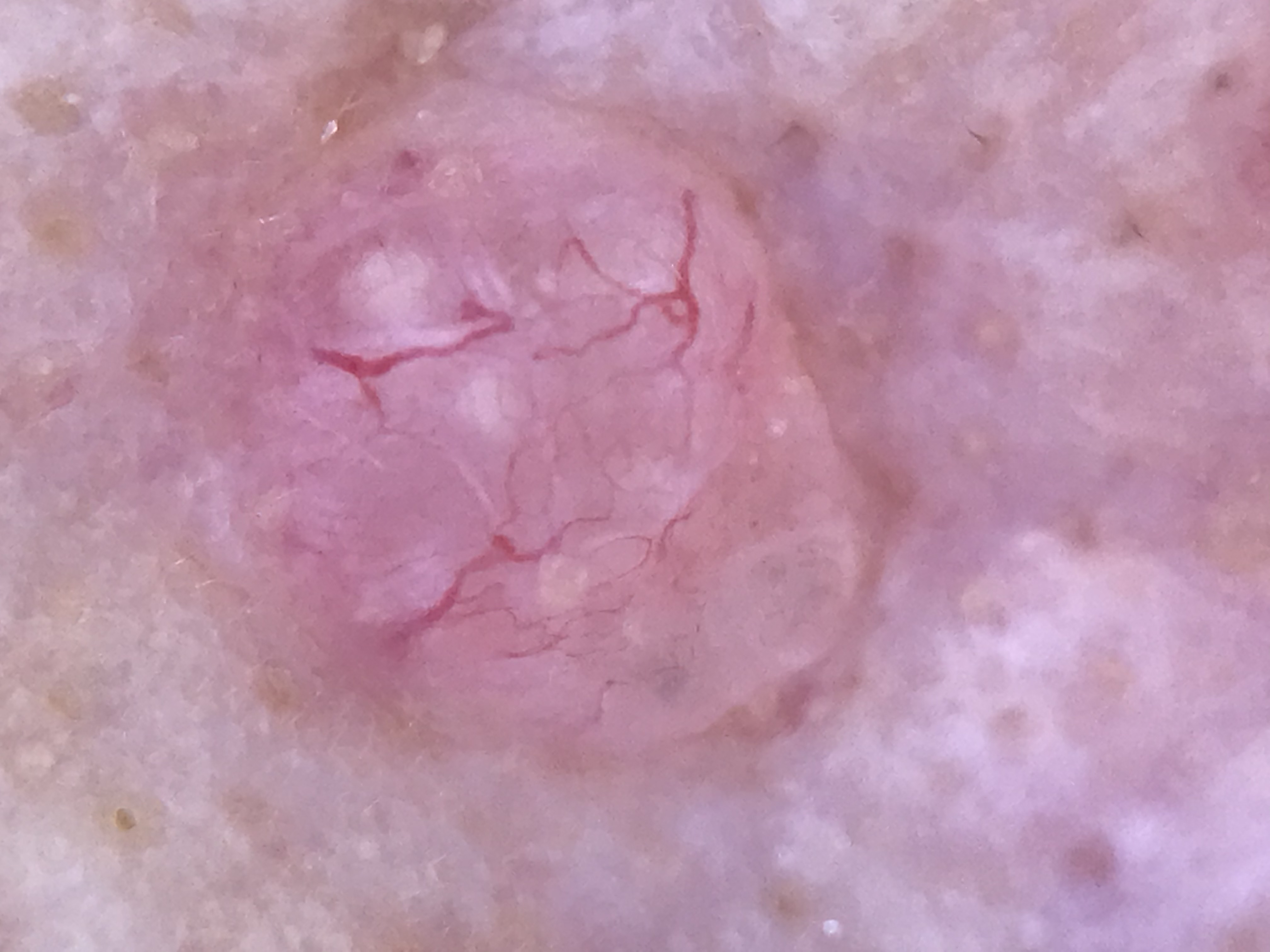Confirmed on histopathology as a basal cell carcinoma.